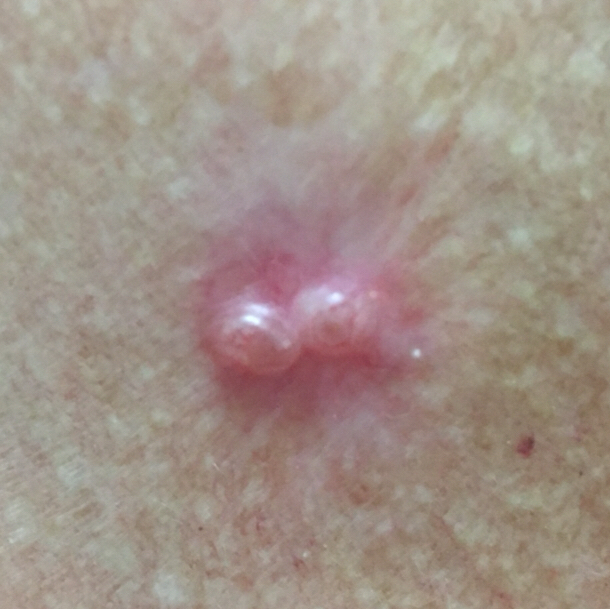Q: What is the imaging modality?
A: clinical photograph
Q: Skin phototype?
A: I
Q: What are the relevant risk factors?
A: prior malignancy (patient or family), no tobacco use
Q: Where on the body is the lesion?
A: the chest
Q: What are the lesion's dimensions?
A: approx. 11 × 6 mm
Q: Any reported symptoms?
A: elevation
Q: What did the workup show?
A: basal cell carcinoma (biopsy-proven)